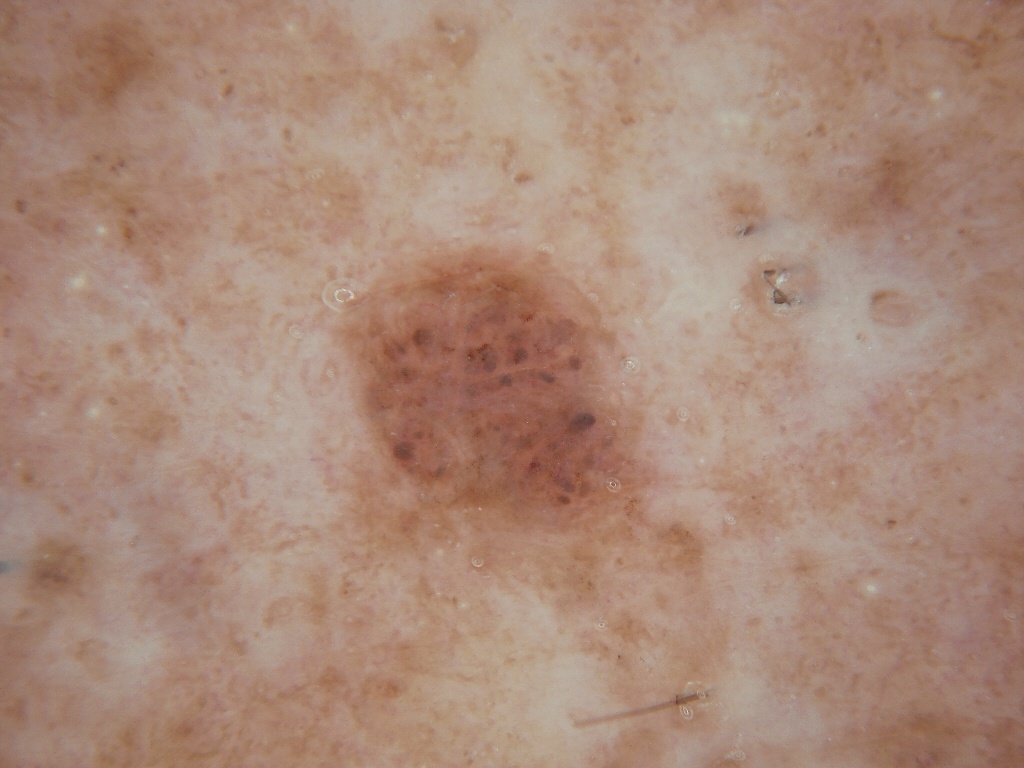Case summary:
The subject is a female approximately 40 years of age. This is a dermoscopic photograph of a skin lesion. With coordinates (x1, y1, x2, y2), lesion location: <box>338, 250, 653, 535</box>. Dermoscopically, the lesion shows globules. The lesion covers approximately 9% of the dermoscopic field.
Assessment:
The clinical diagnosis was a melanocytic nevus, a benign lesion.